A close-up photograph · no constitutional symptoms were reported · the contributor reports bothersome appearance and itching · the affected area is the leg · the patient considered this a rash · the contributor is a male aged 40–49.
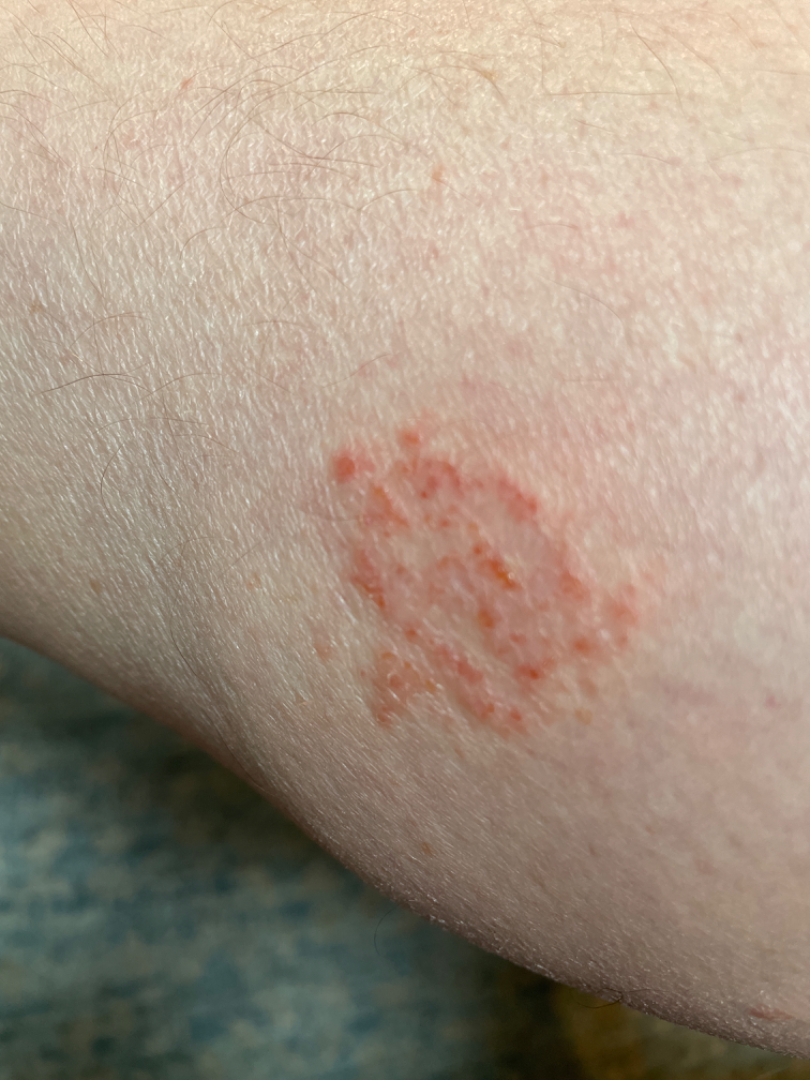Assessment: The skin condition could not be confidently assessed from this image.